The photo was captured at an angle, located on the arm and leg.
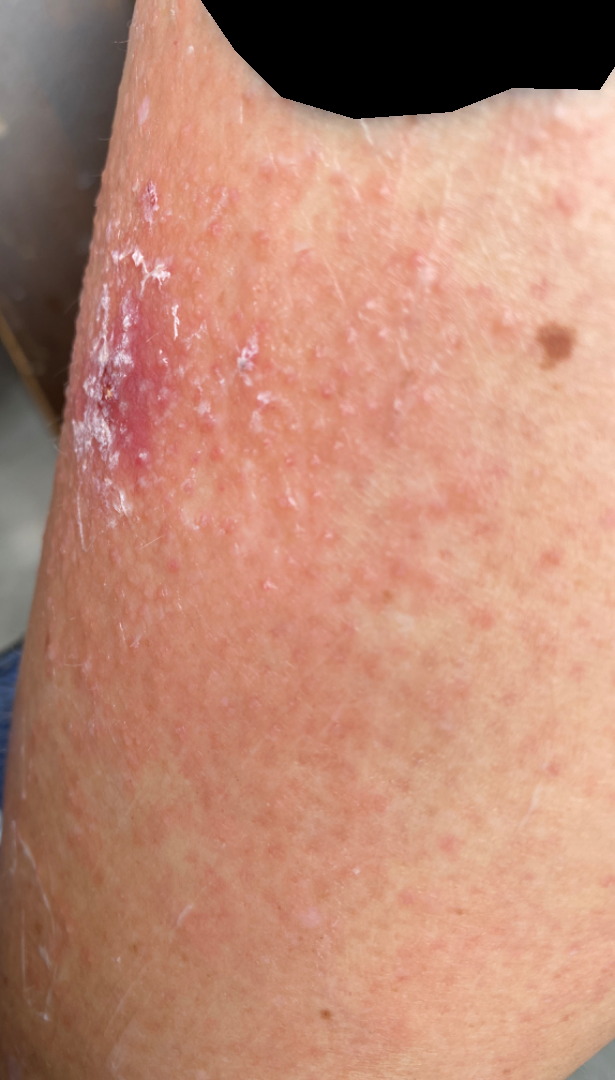Findings:
• lesion symptoms — enlargement, bothersome appearance and itching
• present for — less than one week
• skin tone — Fitzpatrick III
• assessment — Impetigo and Allergic Contact Dermatitis were each considered, in no particular order